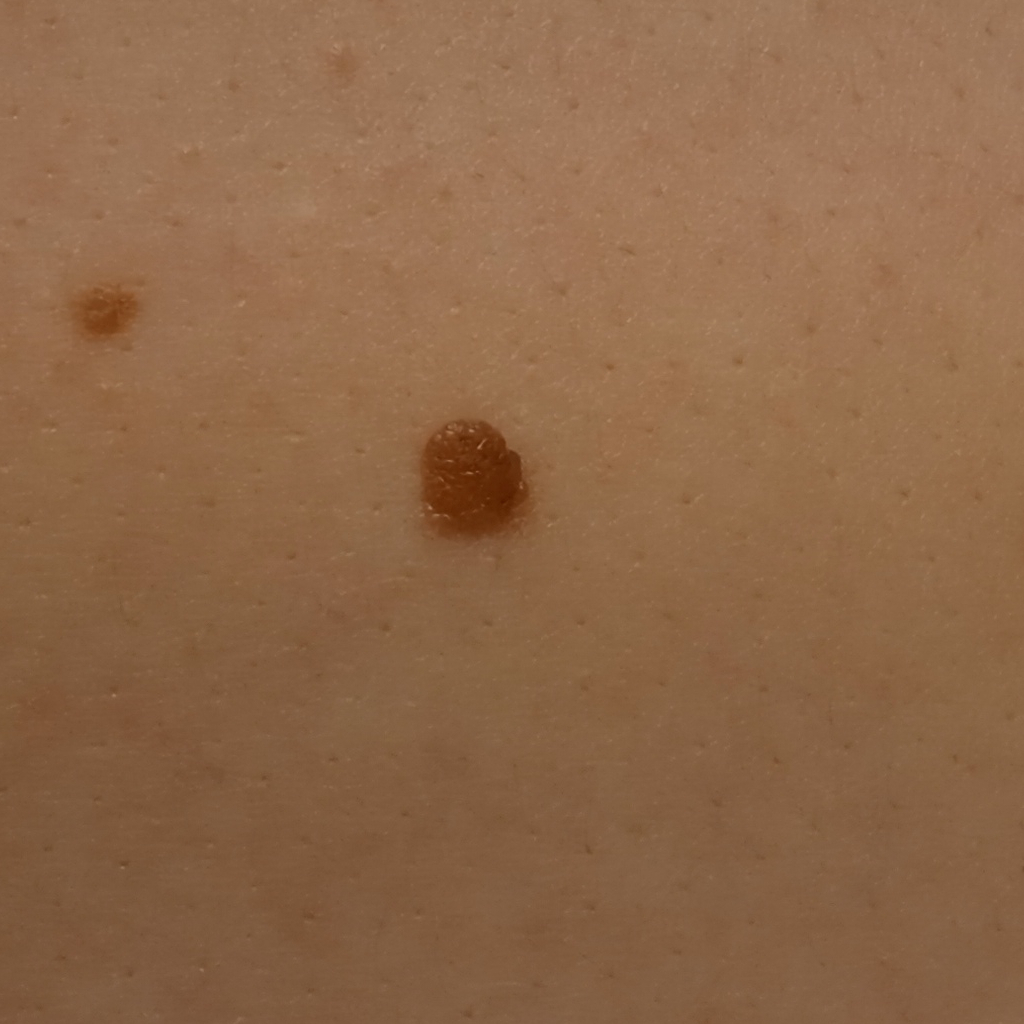Imaged for a research study, with no referral diagnosis recorded. A clinical close-up of a skin lesion. The patient says their skin reddens with sun exposure. On a questionnaire the patient reported a history of sunbed use, no prior organ transplant, and no personal history of cancer. A female patient aged 26. Located on the back. The lesion measures approximately 5.5 mm. The lesion was assessed as a melanocytic nevus.